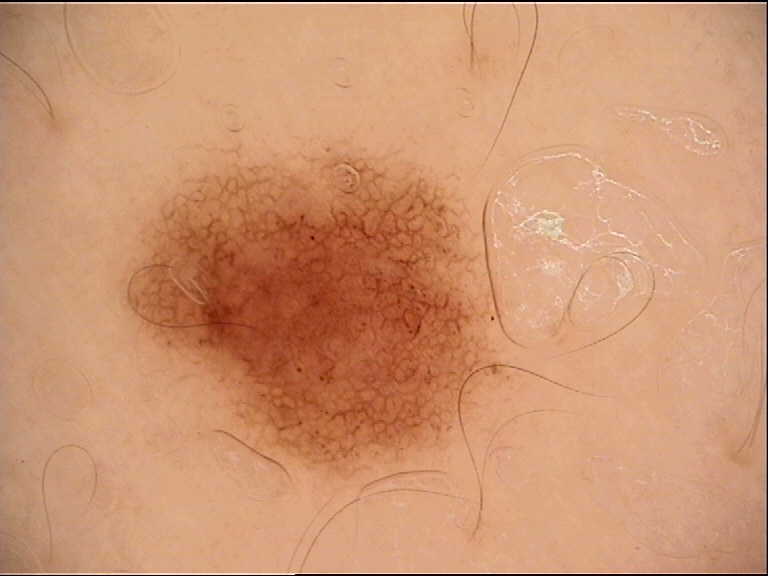diagnosis = dysplastic junctional nevus (expert consensus)